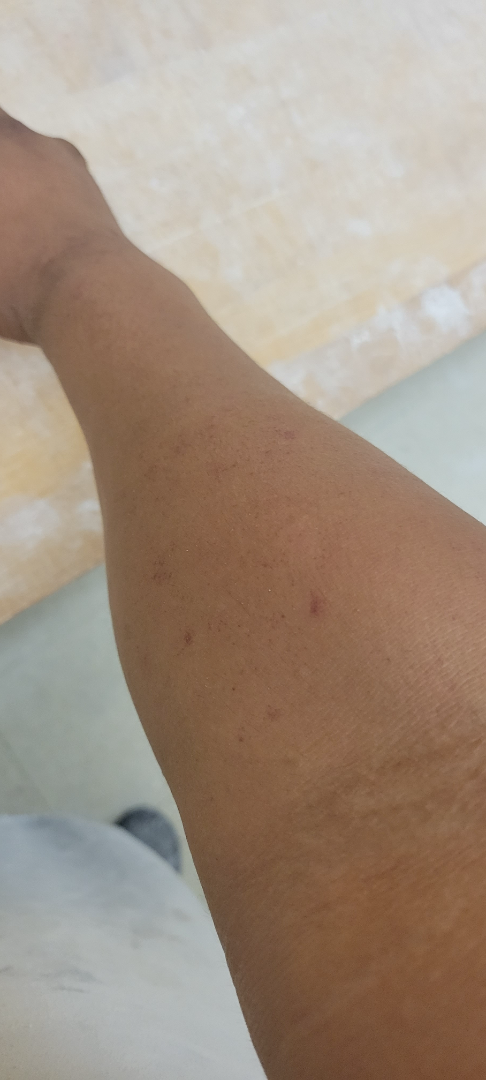The differential includes Pigmented purpuric eruption and Leukocytoclastic Vasculitis, with no clear leading consideration.